A female subject, aged 63 to 67 · this is a dermoscopic photograph of a skin lesion:
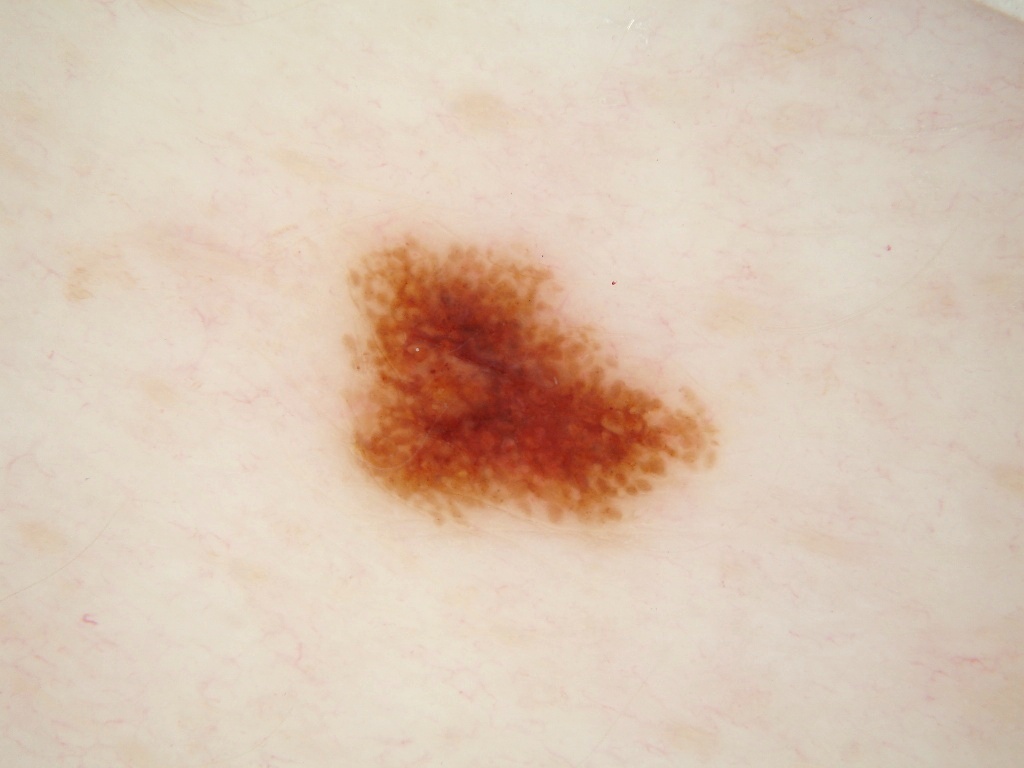{"lesion_location": {"bbox_xyxy": [327, 226, 735, 540]}, "dermoscopic_features": {"present": ["globules", "pigment network"], "absent": ["negative network", "streaks", "milia-like cysts"]}, "lesion_extent": "moderate", "diagnosis": {"name": "melanoma", "malignancy": "malignant", "lineage": "melanocytic", "provenance": "histopathology"}}